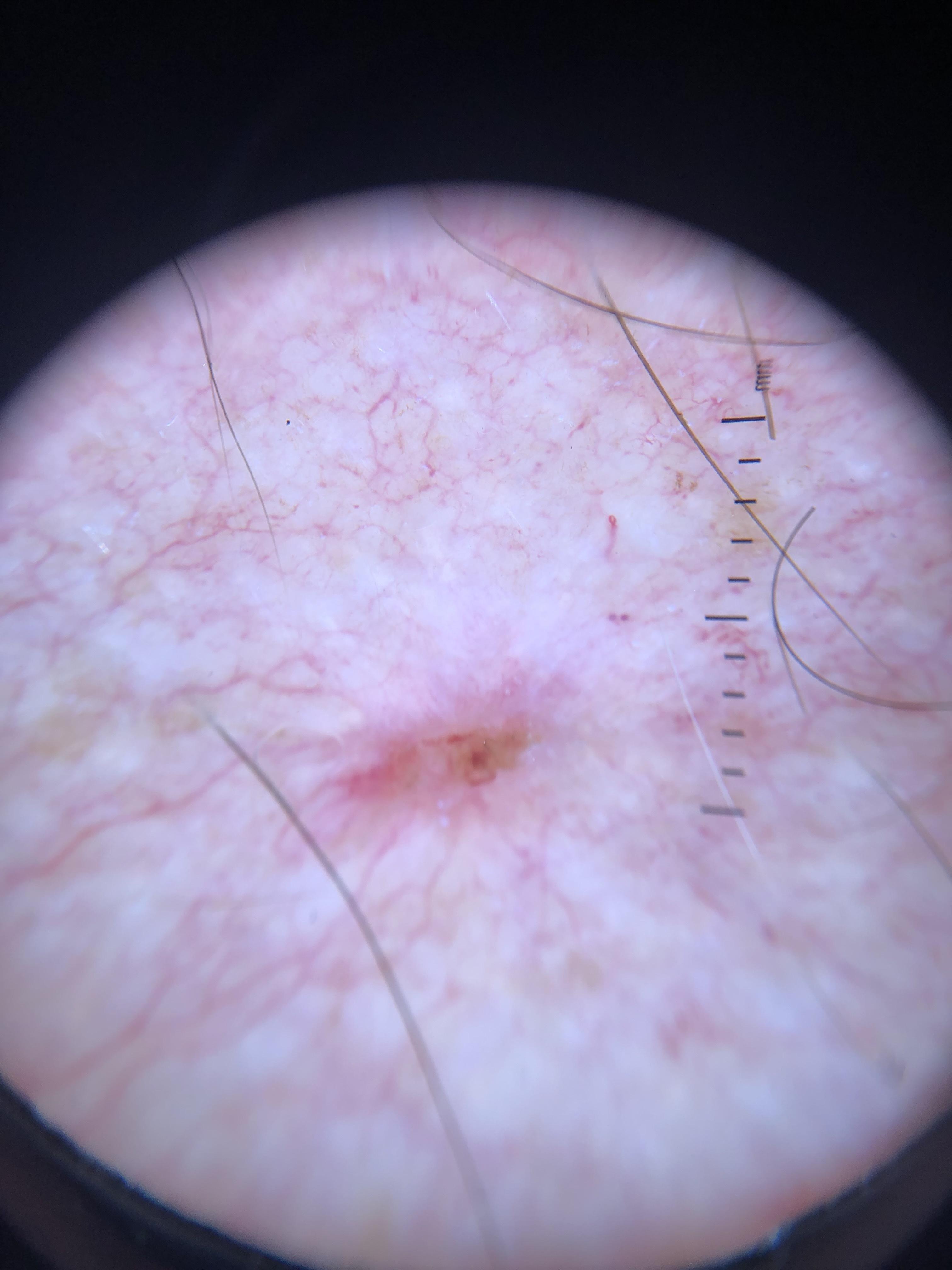Case:
- modality — dermoscopic image
- anatomic site — the trunk
- diagnosis — Basal cell carcinoma (biopsy-proven)